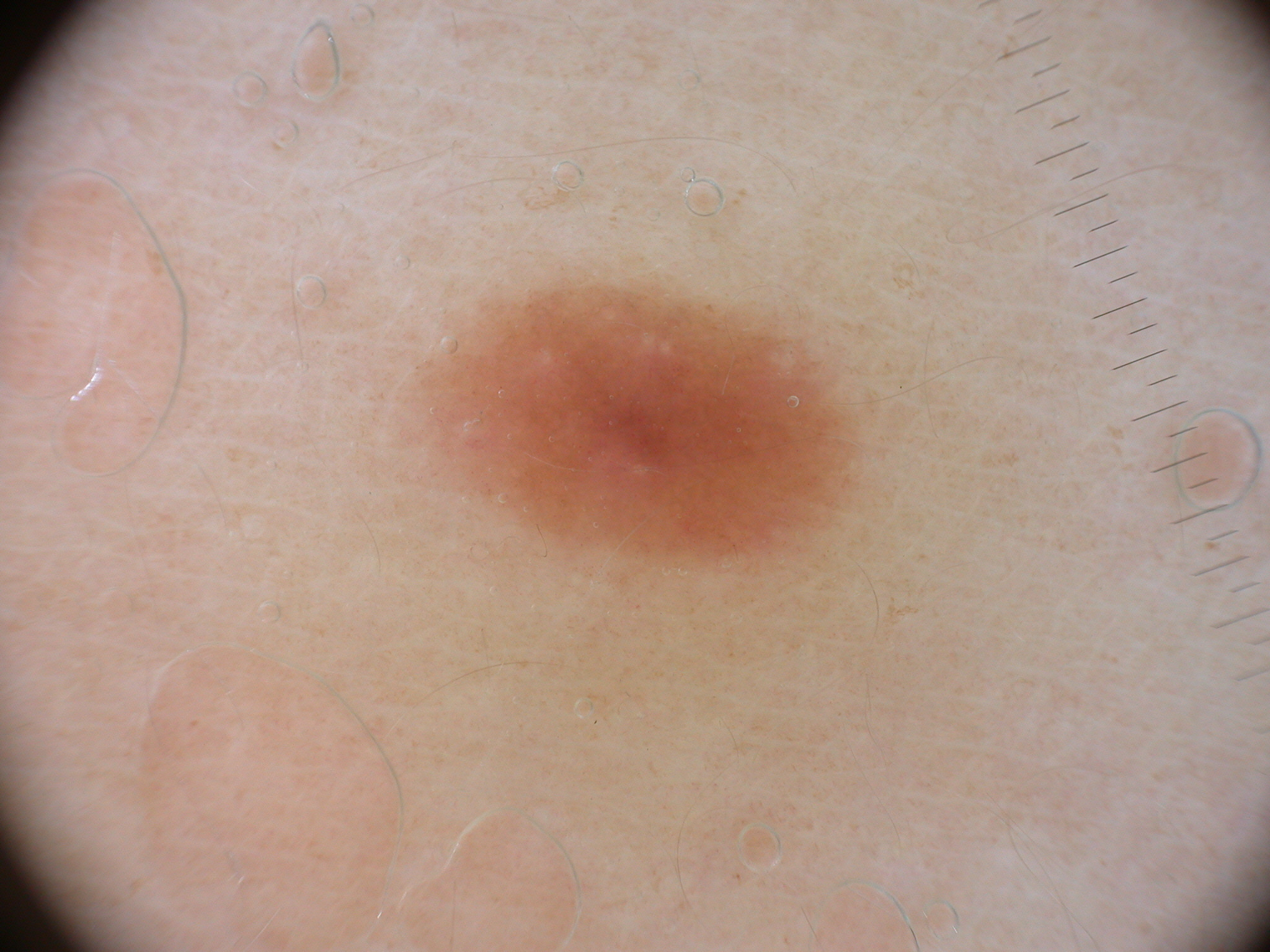Case summary:
– modality: dermoscopic image
– lesion bbox: [383,266,889,589]
– absent dermoscopic findings: milia-like cysts, globules, negative network, streaks, and pigment network
– impression: a melanocytic nevus